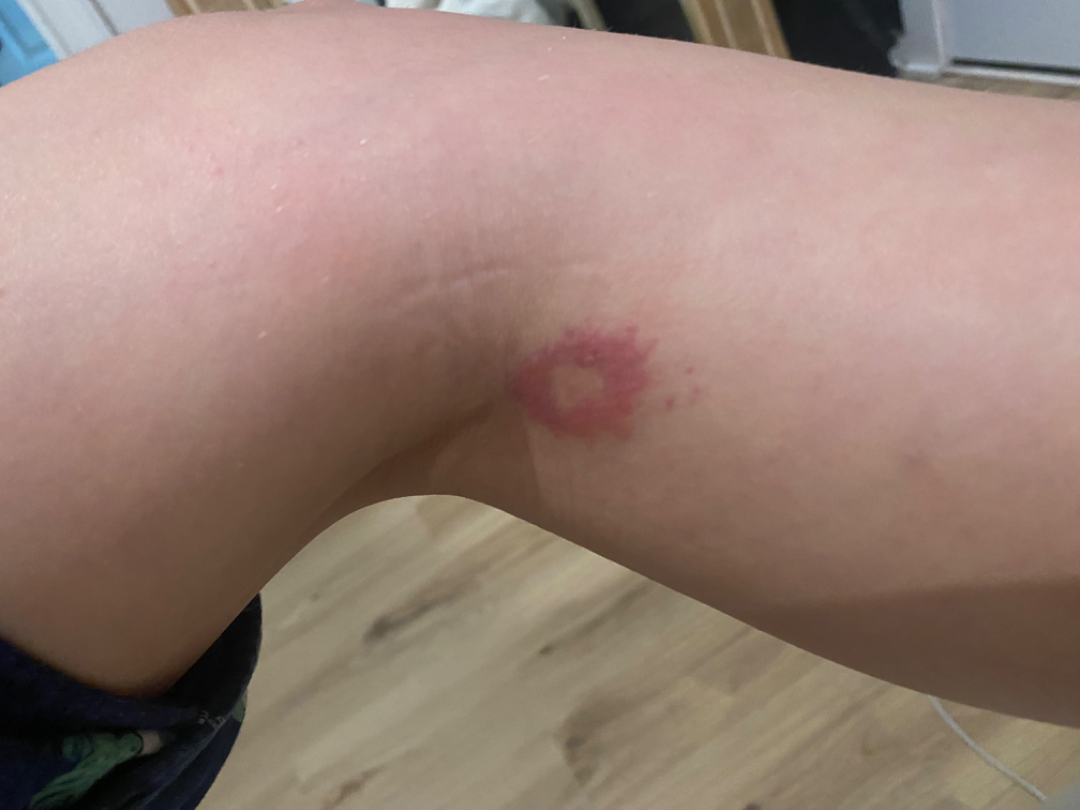Review: The condition could not be reliably identified from the image. Patient information: The subject is a female aged 18–29. The lesion involves the leg. Close-up view.